The photograph is a close-up of the affected area:
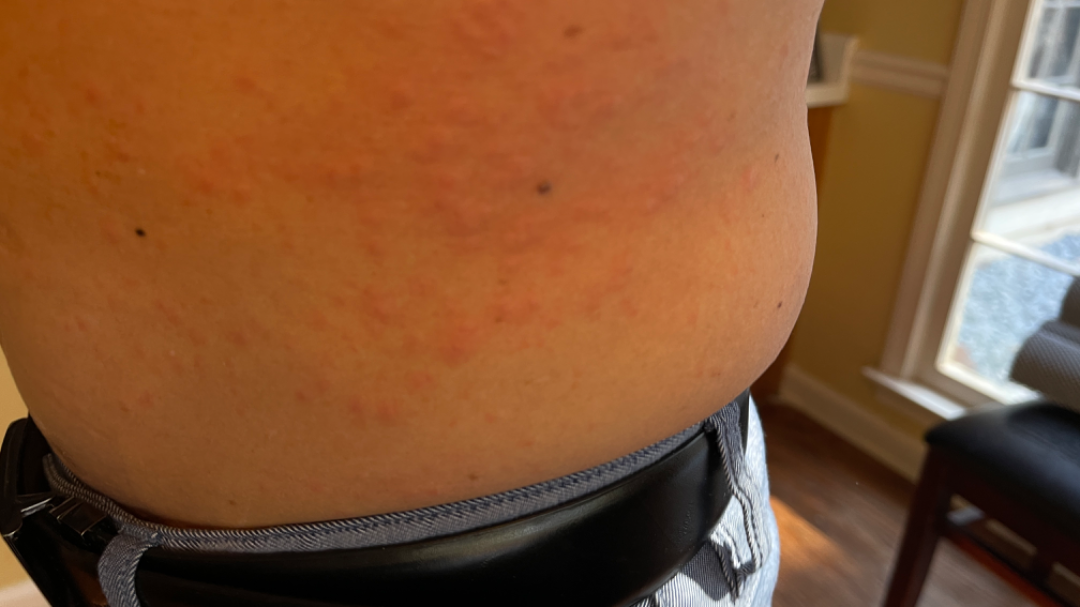Findings:
Most consistent with Urticaria.